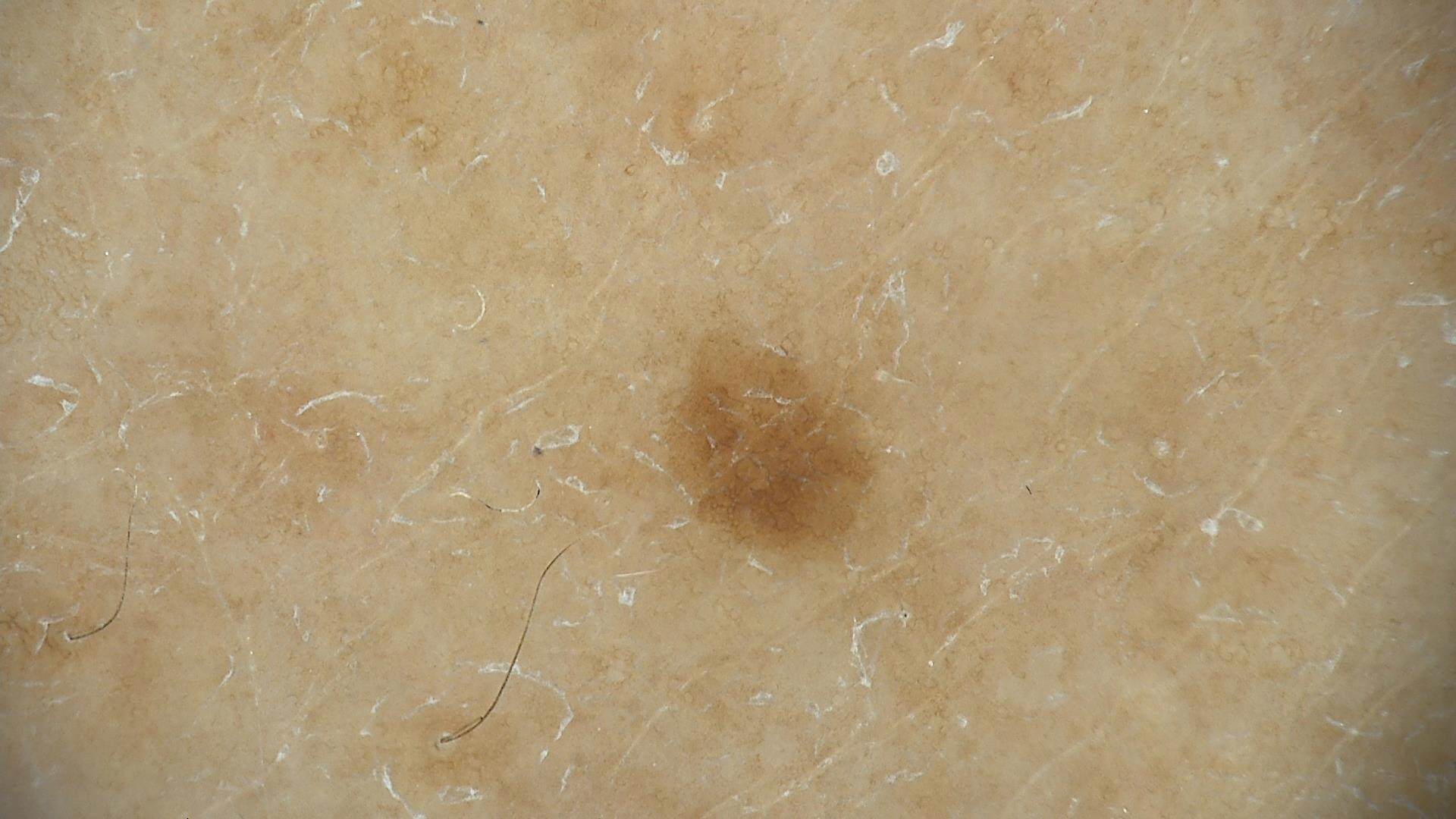Case:
* label — solar lentigo (expert consensus)